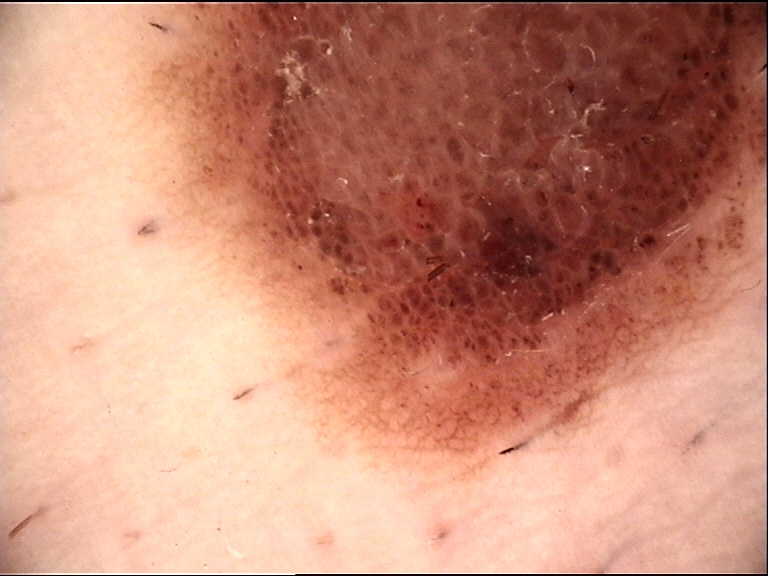The morphology is that of a banal lesion. Labeled as a compound nevus.